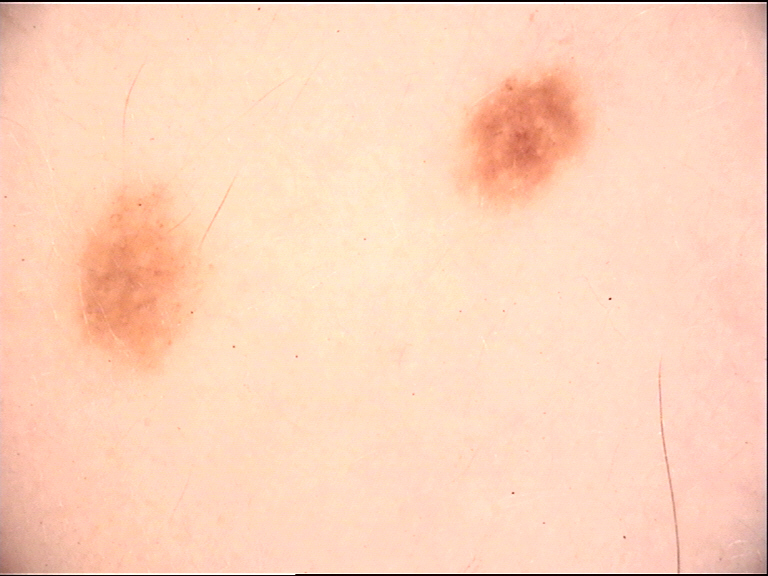image type: dermoscopy | category: compound, banal | diagnostic label: Miescher nevus (expert consensus).